This image was taken at an angle · the palm is involved · texture is reported as raised or bumpy and rough or flaky · the patient considered this a rash · the condition has been present for one to four weeks · symptoms reported: burning and itching: 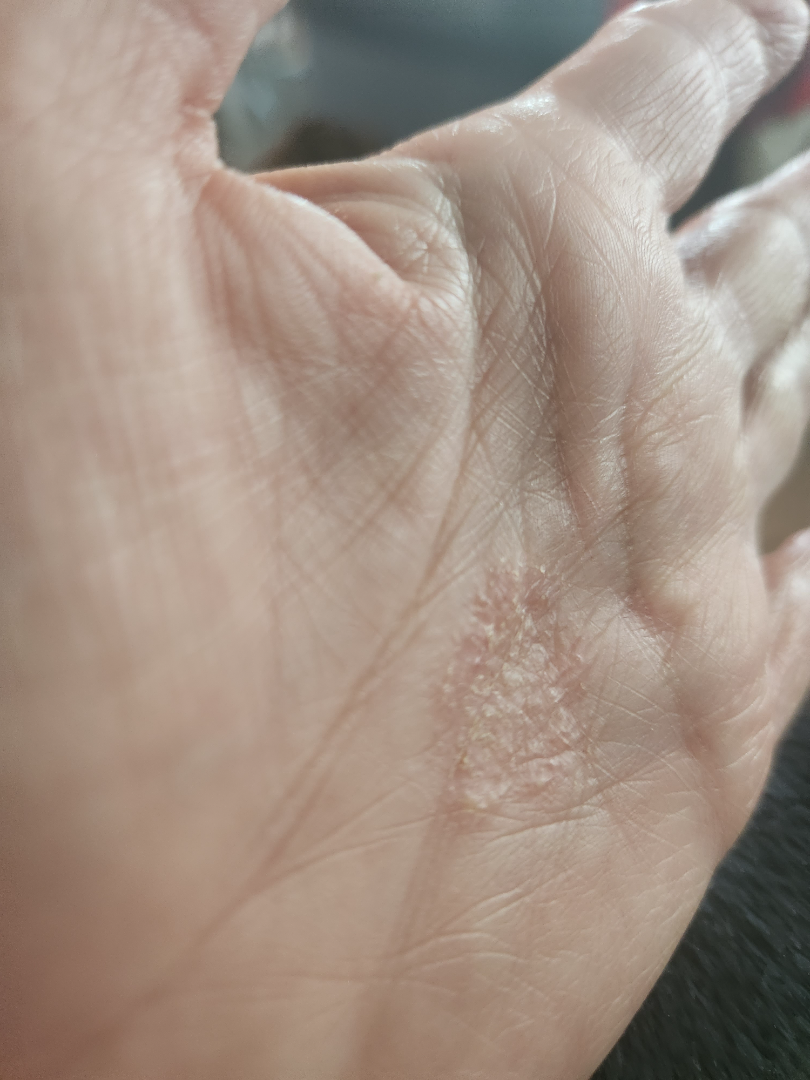Impression: The reviewing dermatologist's impression was: the differential, in no particular order, includes Psoriasis and Eczema.